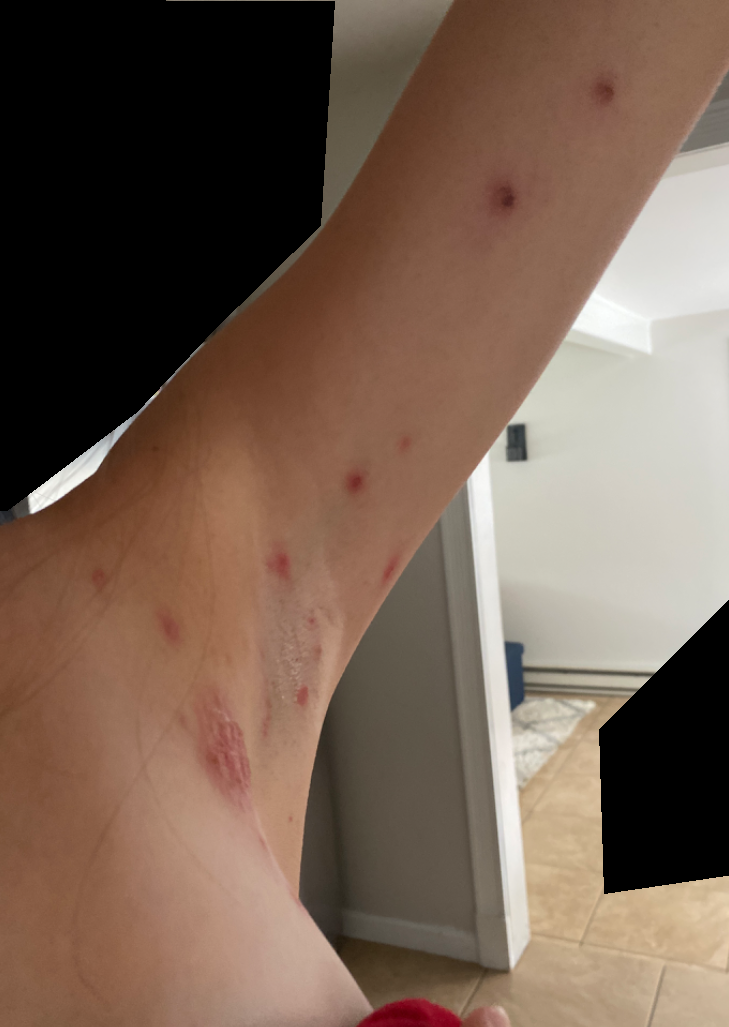Reported duration is less than one week. Skin tone: FST II; human graders estimated MST 2 or 3 (two reviewer pools). The arm is involved. An image taken at a distance. On remote review of the image, the impression is Impetigo.